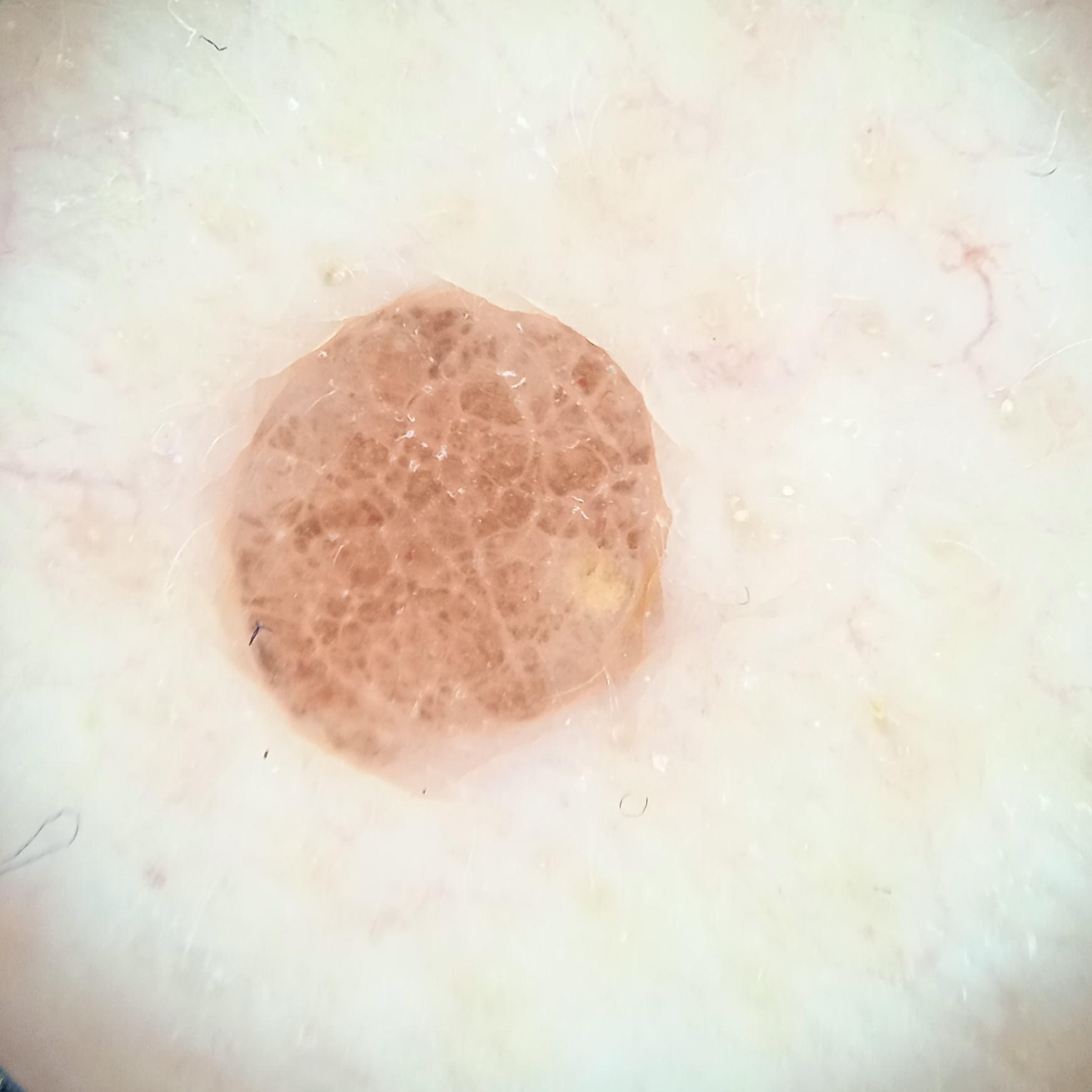The patient describes having numerous moles.
Dermoscopy of a skin lesion.
By self-report, immunosuppression, a personal history of skin cancer, and a family history of skin cancer.
The lesion involves an arm.
The lesion is about 3 mm across.
Dermatologist review favored a melanocytic nevus.